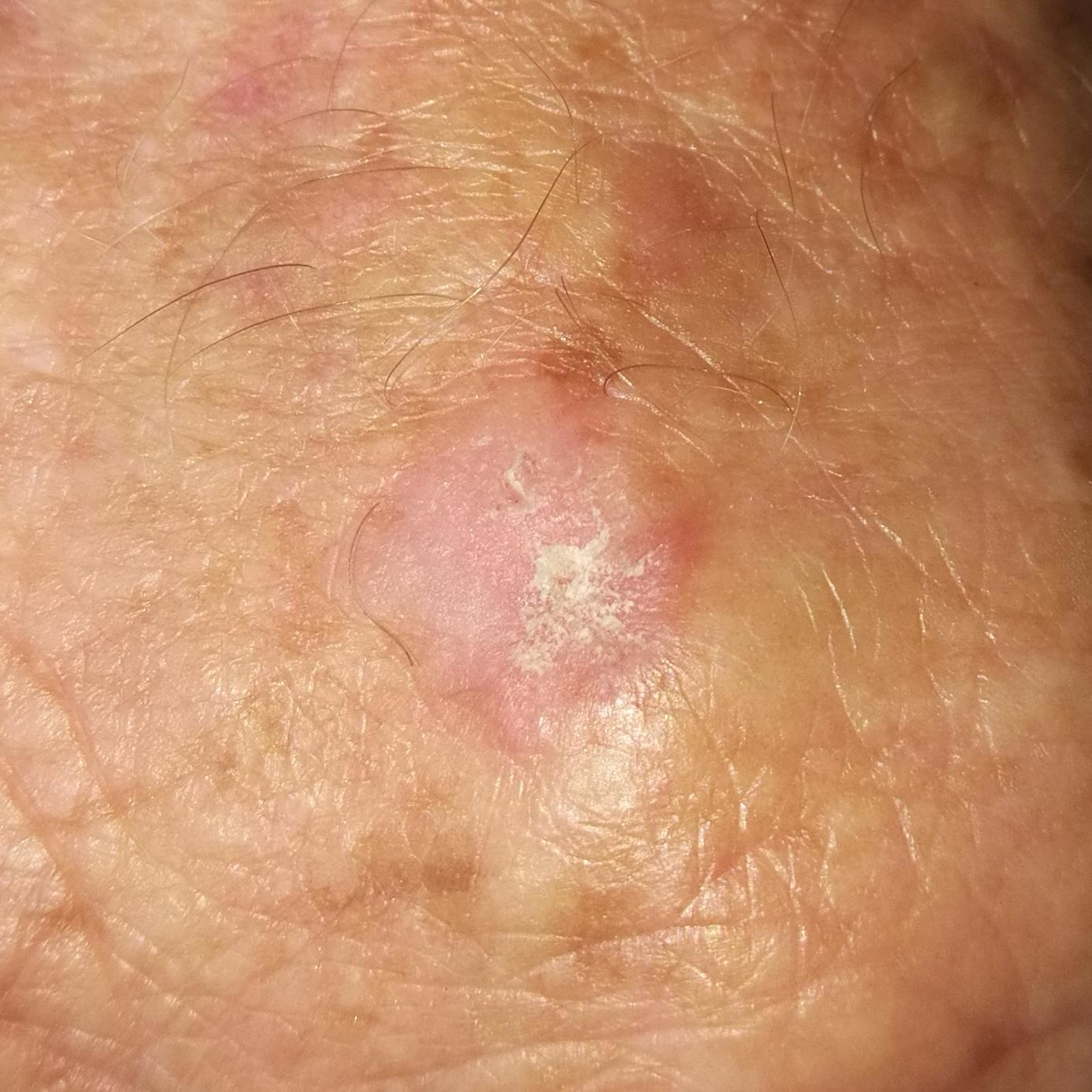The diagnostic impression was an actinic keratosis.